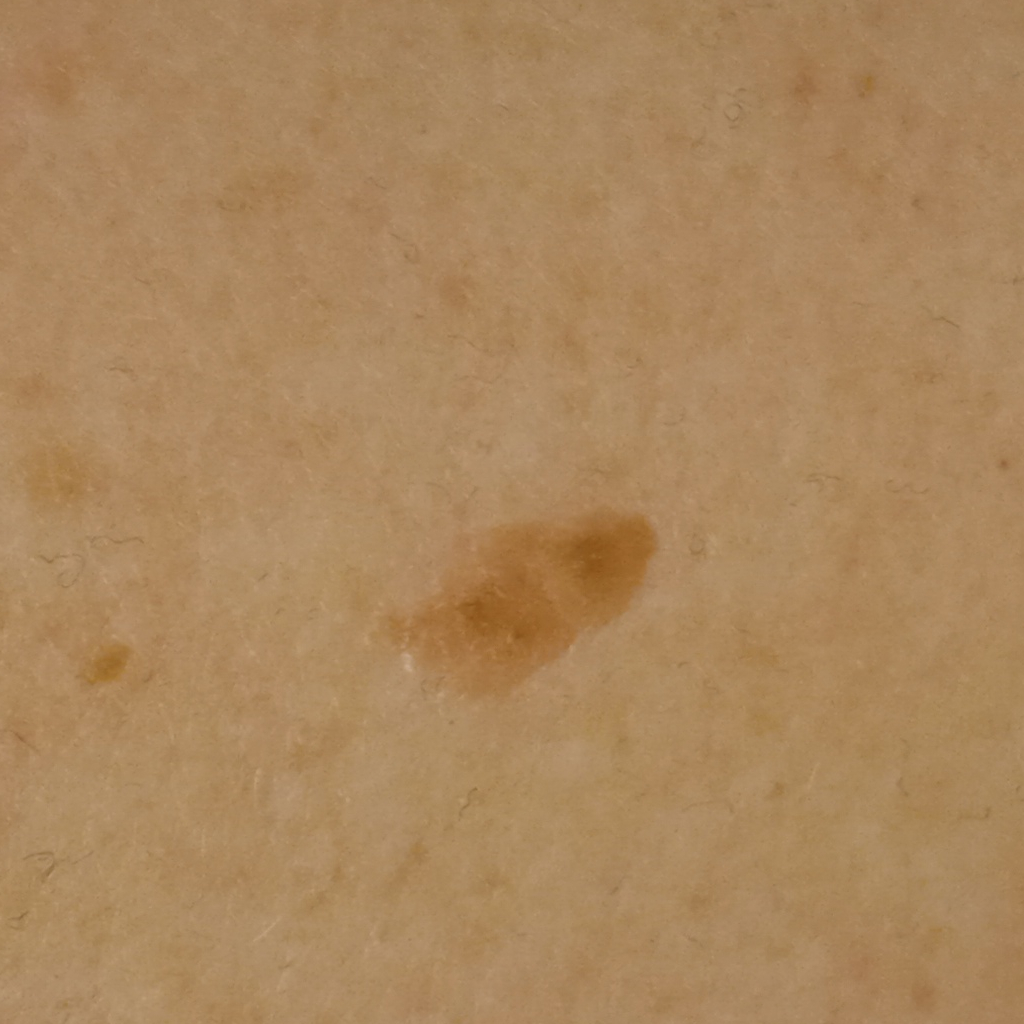image: clinical photograph; clinical context: research study (no referral diagnosis); sun reaction: skin reddens with sun exposure; location: the torso; assessment: seborrheic keratosis (dermatologist consensus).